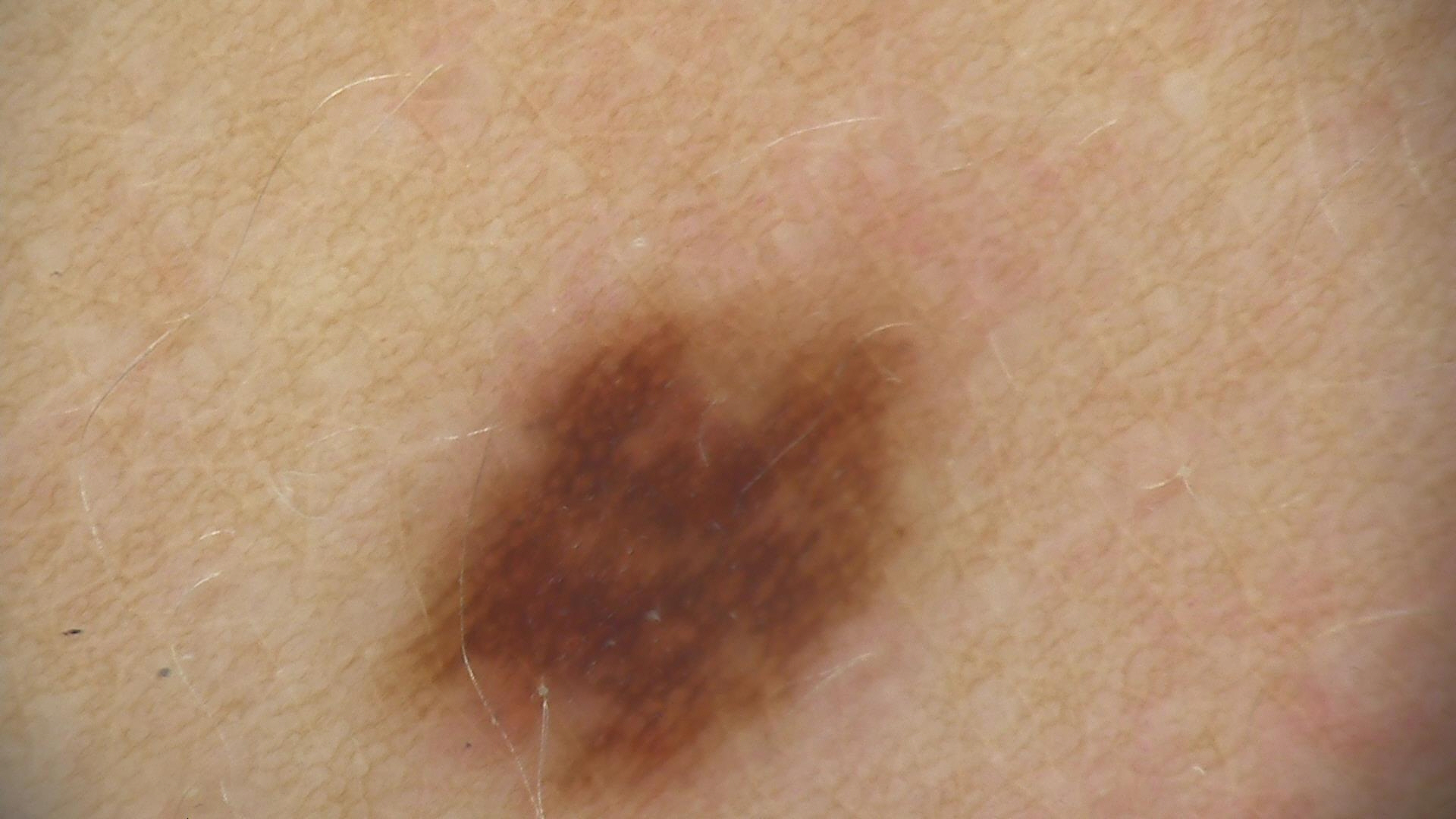Findings:
• diagnosis — dysplastic junctional nevus (expert consensus)